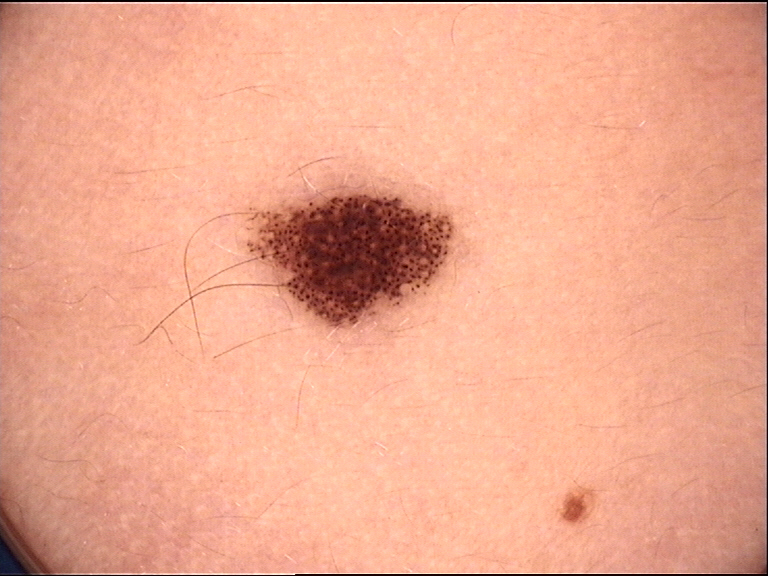assessment = compound nevus (expert consensus).